The contributor is male; the top or side of the foot and leg are involved; a close-up photograph:
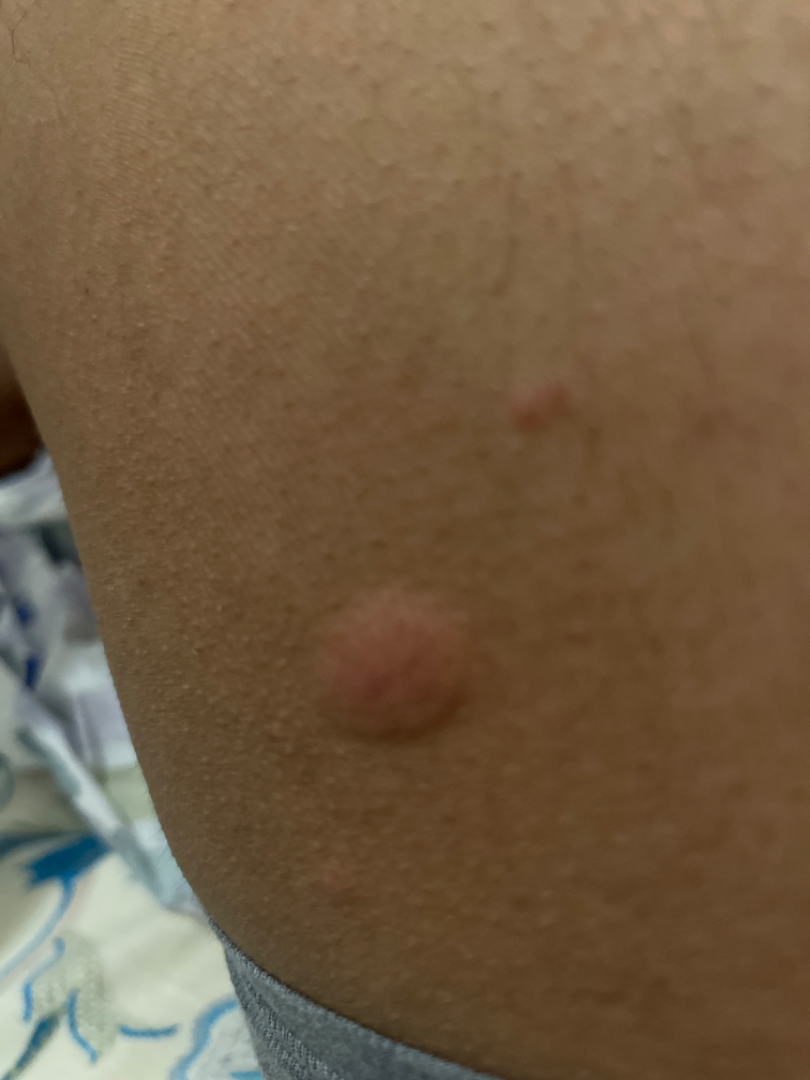Review: On remote review of the image, Insect Bite and Urticaria were considered with similar weight; with consideration of Allergic Contact Dermatitis.